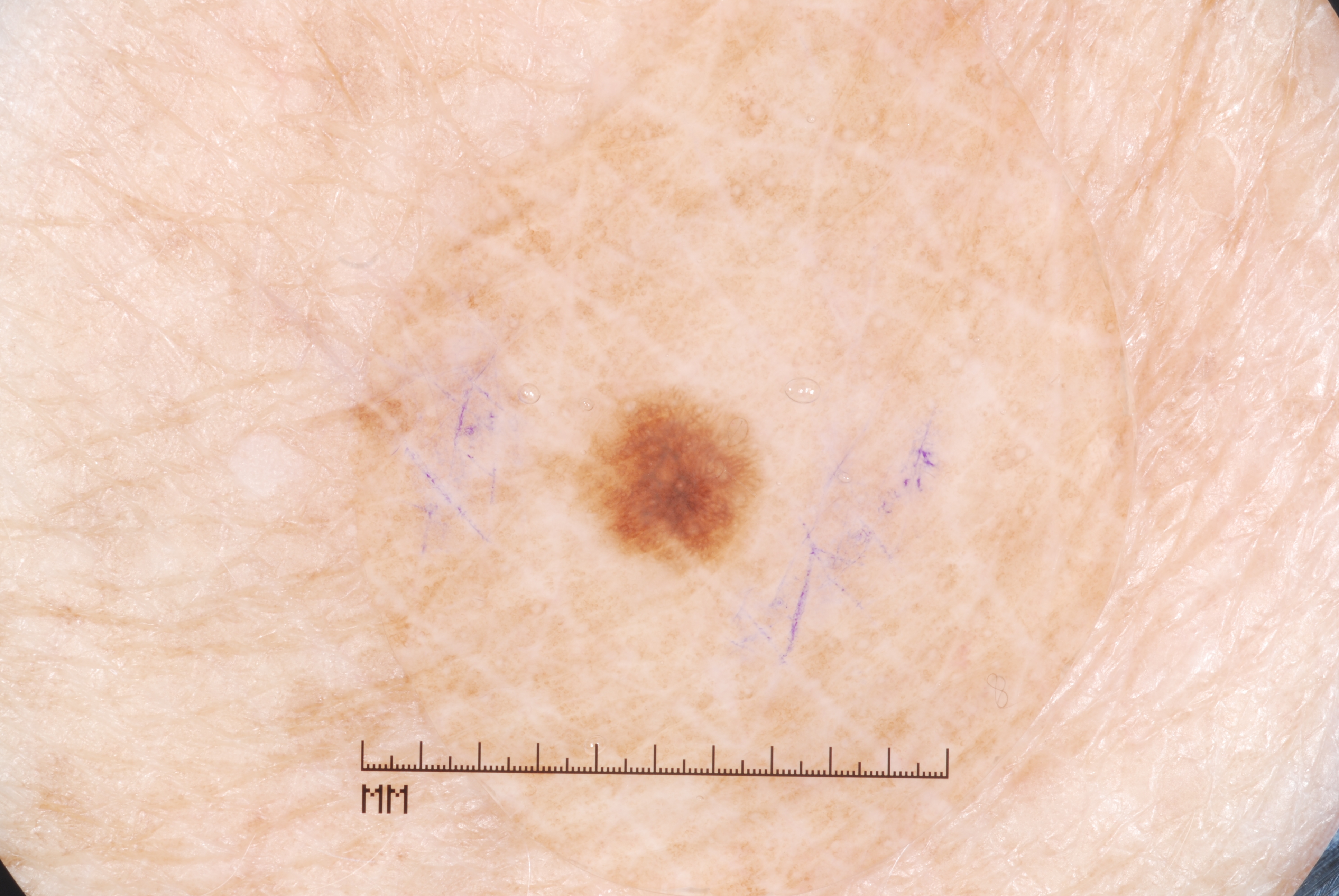A dermatoscopic image of a skin lesion.
The patient is a female roughly 80 years of age.
The dermoscopic pattern shows pigment network.
In (x1, y1, x2, y2) order, the lesion spans <bbox>535, 383, 766, 577</bbox>.
The diagnostic assessment was a melanocytic nevus, a benign skin lesion.